A male subject 67 years of age. The patient was assessed as Fitzpatrick phototype II. A clinical photograph of a skin lesion.
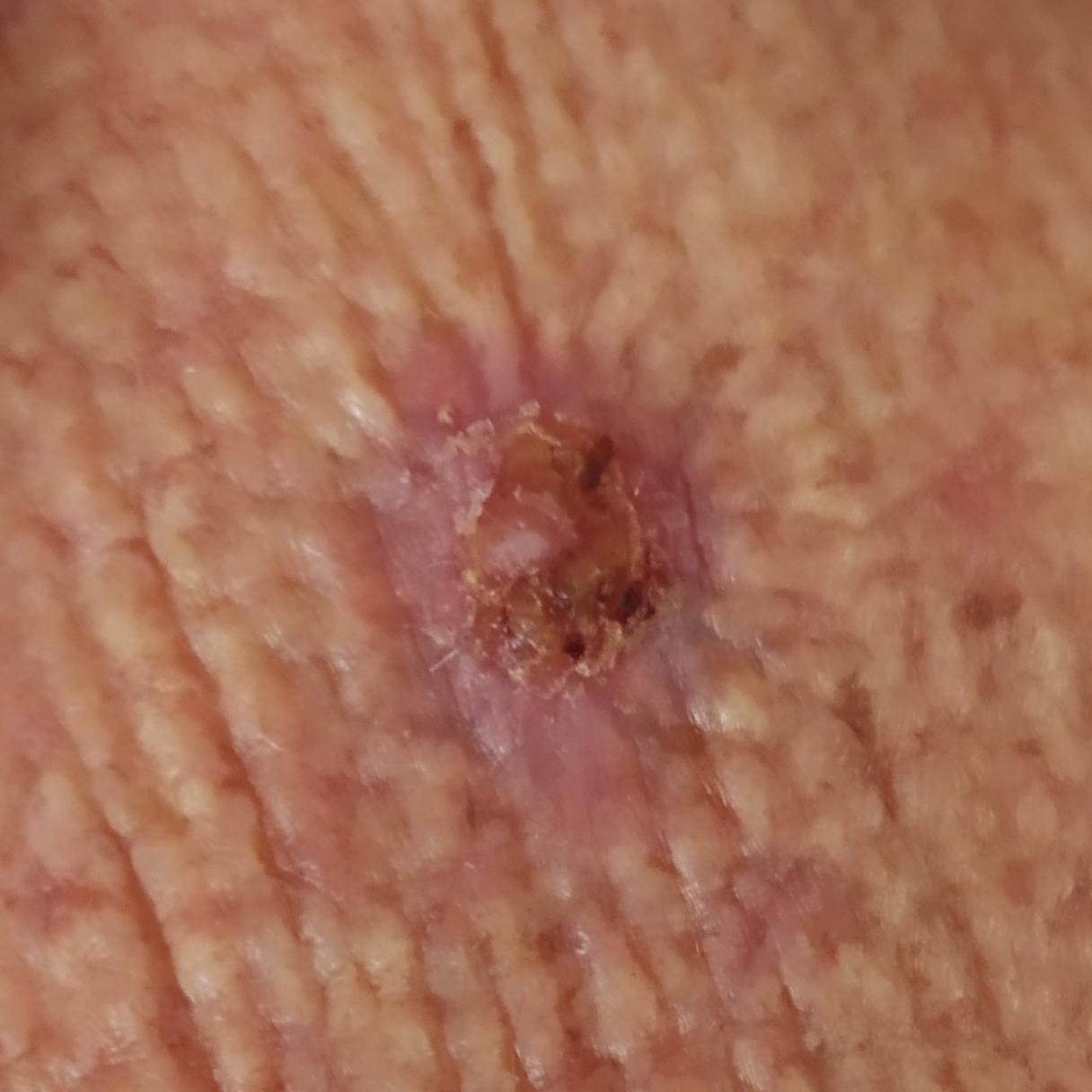Q: What is the anatomic site?
A: an arm
Q: How large is the lesion?
A: 15 × 11 mm
Q: What symptoms does the patient report?
A: itching, elevation, bleeding / no pain
Q: What is this lesion?
A: basal cell carcinoma (biopsy-proven)